The subject is a male aged 30–39. An image taken at a distance. The affected area is the front of the torso and back of the torso — 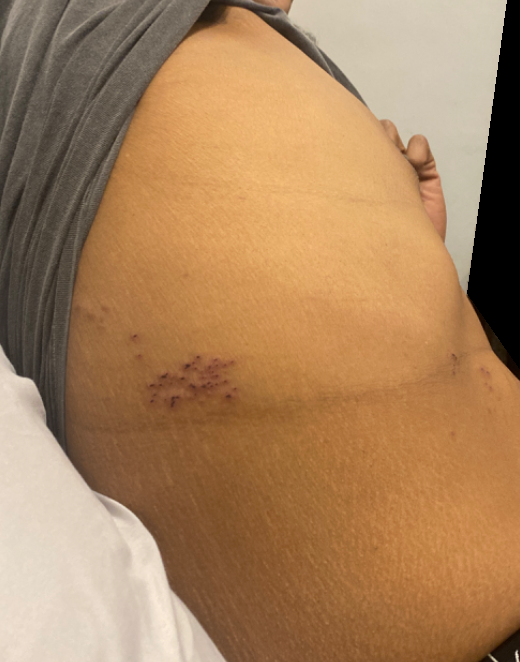  texture: raised or bumpy
  symptoms:
    - enlargement
    - bothersome appearance
    - itching
    - pain
    - burning
  systemic_symptoms: none reported
  duration: one to four weeks
  patient_category: a rash
  differential:
    leading:
      - Herpes Simplex
    considered:
      - Herpes Zoster
      - Lymphangioma
    unlikely:
      - Dermatitis herpetiformis